A subject 31 years old · a clinical close-up photograph of a skin lesion — 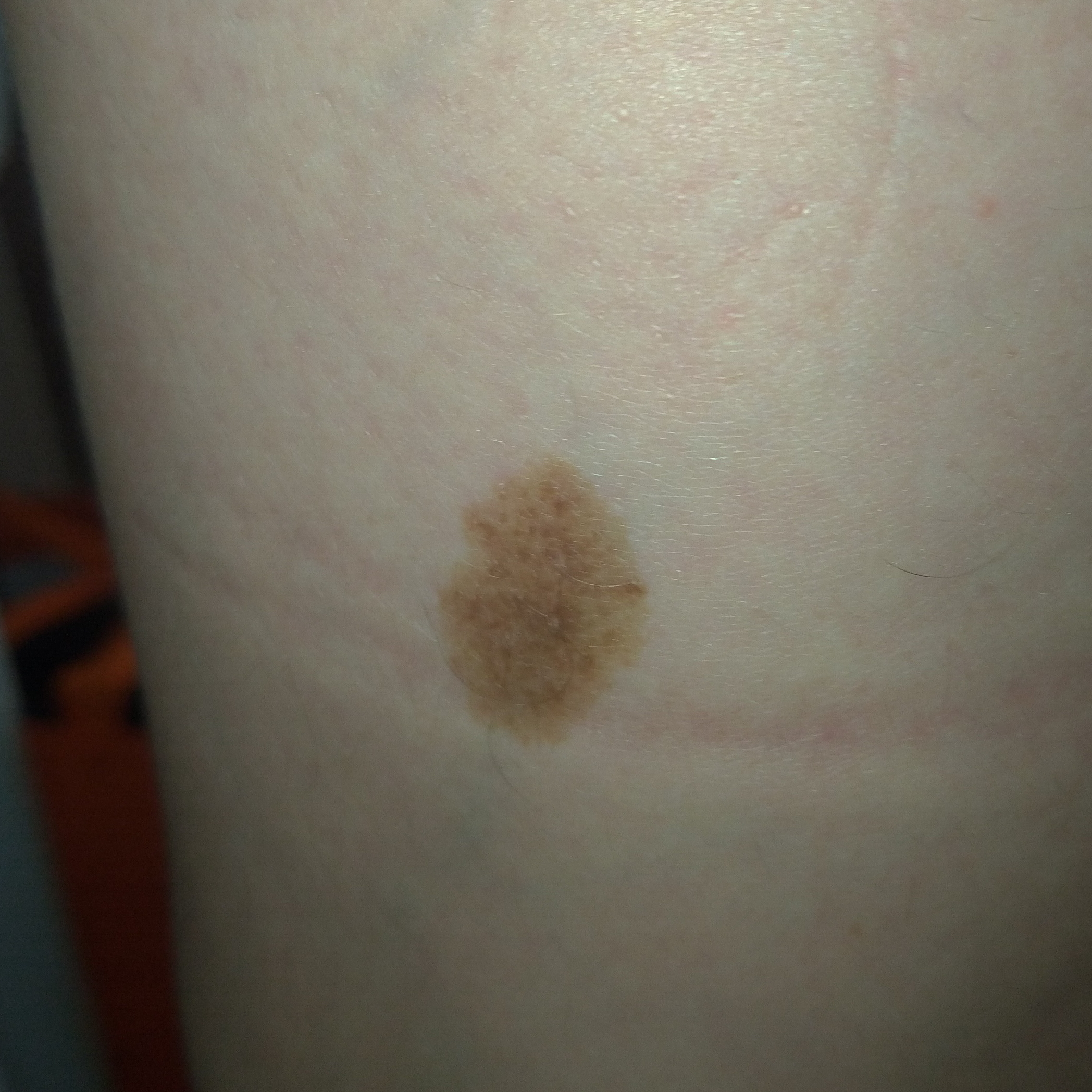patient-reported symptoms: growth / no pain; impression: nevus (clinical consensus).